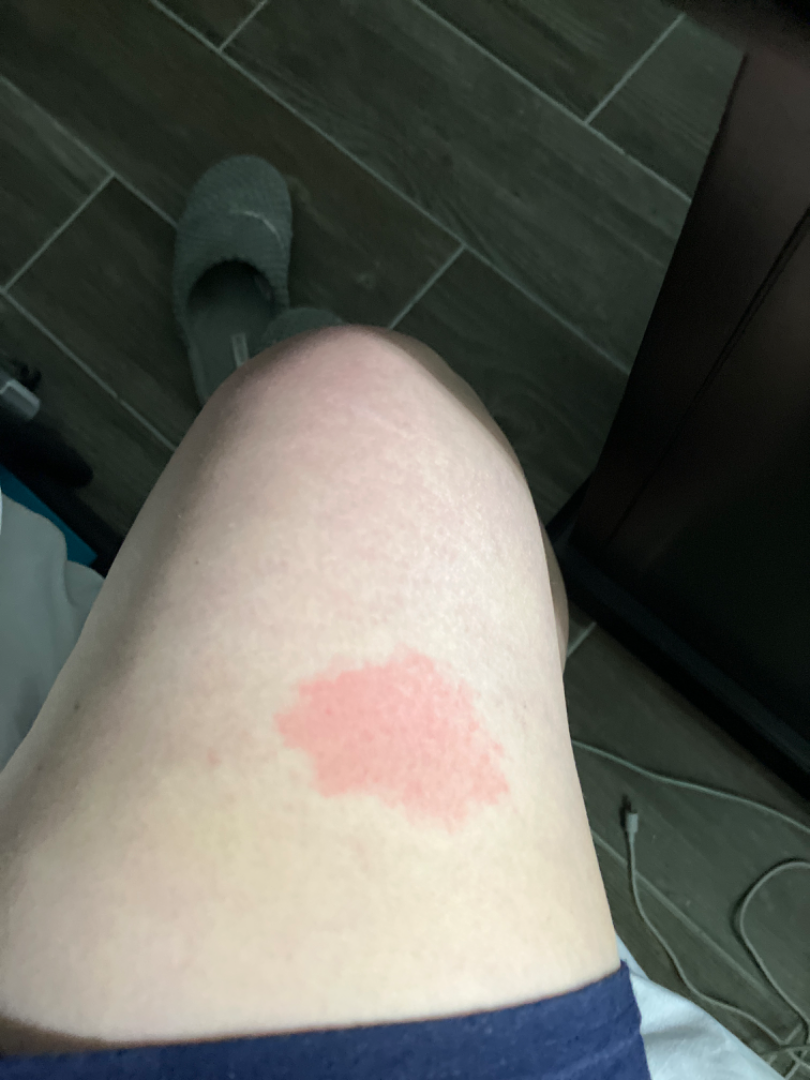• duration — less than one week
• framing — at a distance
• anatomic site — leg
• texture — raised or bumpy
• symptoms — bothersome appearance
• constitutional symptoms — none reported
• dermatologist impression — single-reviewer assessment: the differential is split between Allergic Contact Dermatitis and Erythema migrans